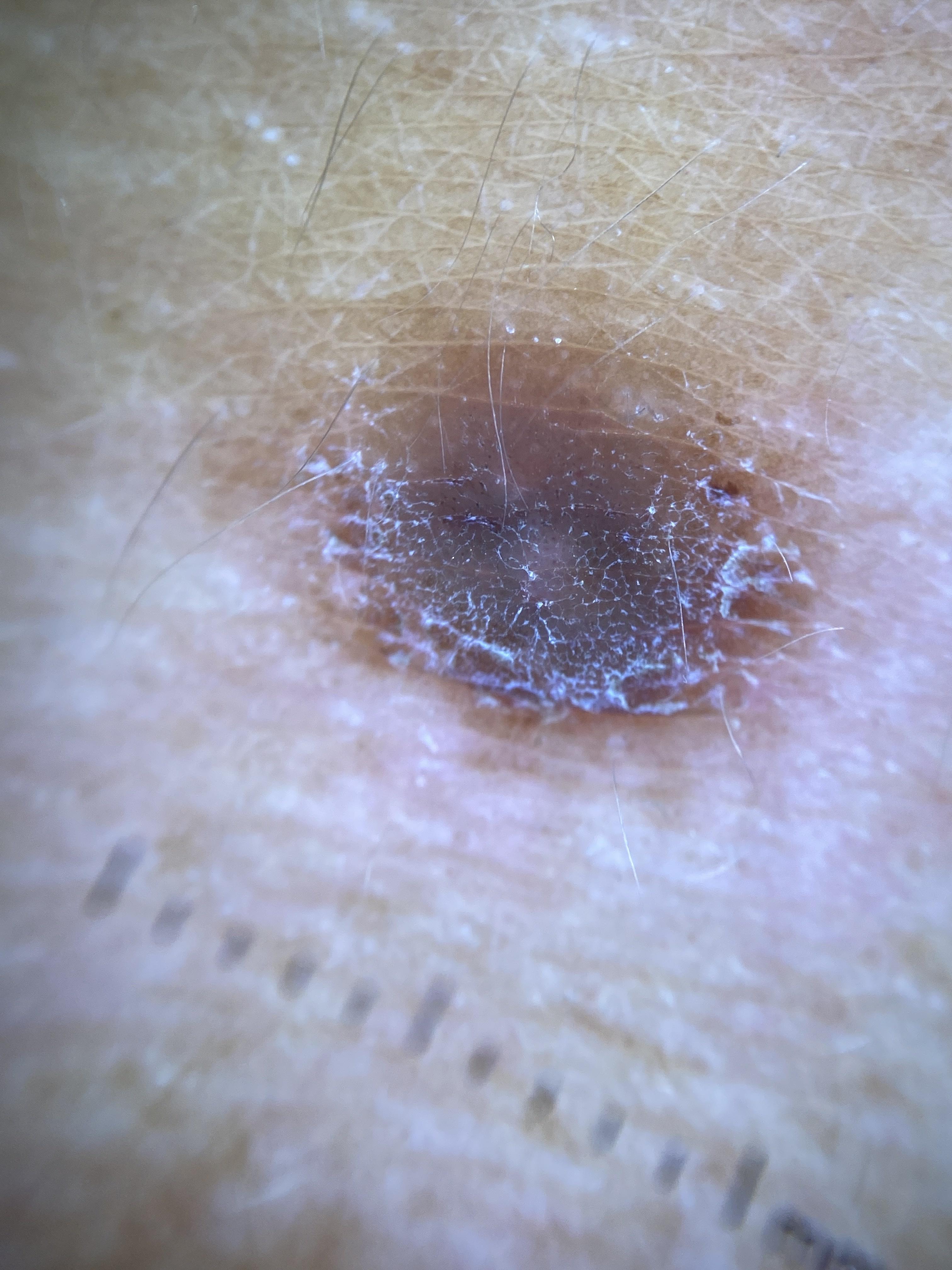Conclusion:
The biopsy diagnosis was a dermatofibroma.